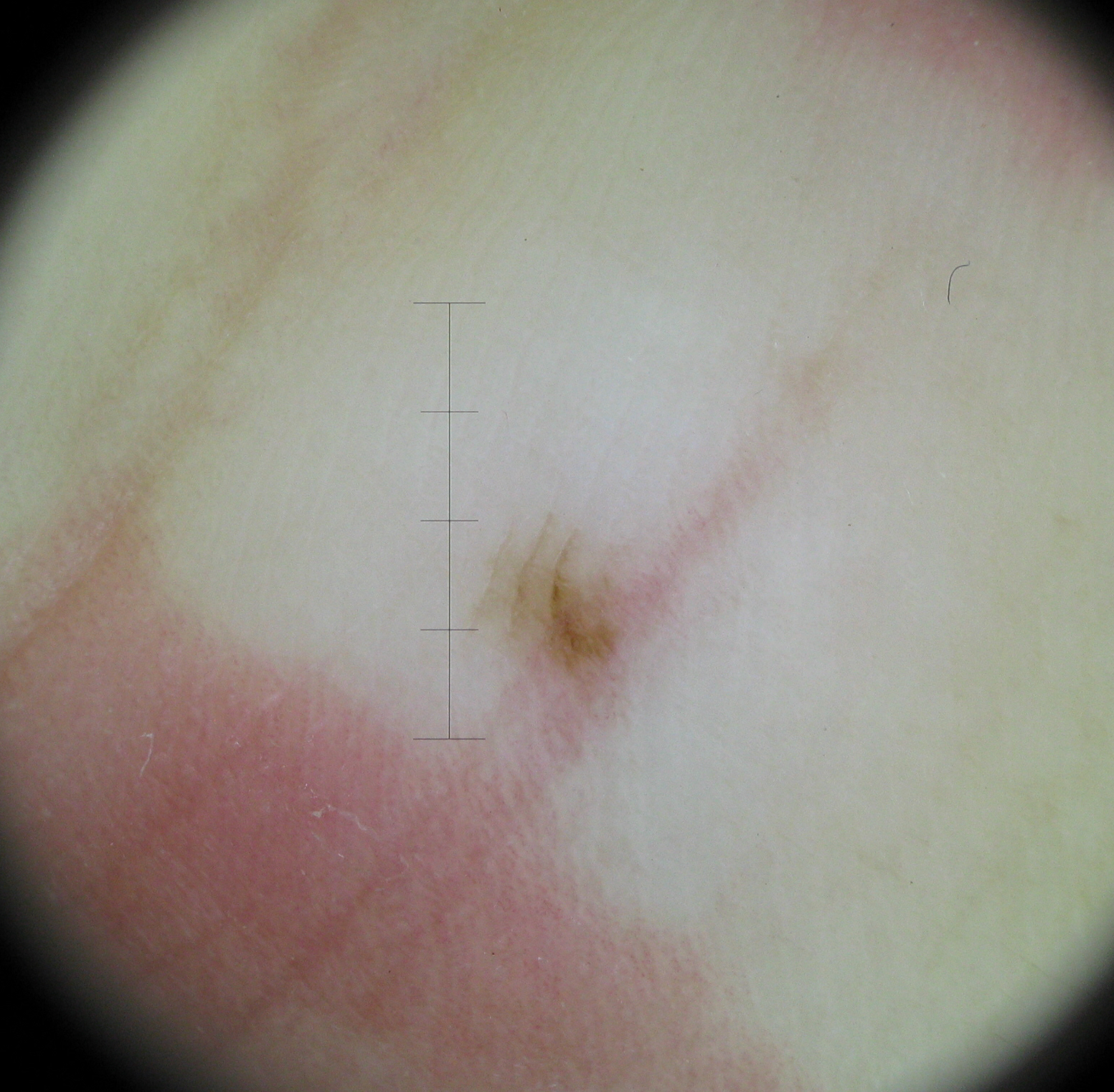Labeled as an acral junctional nevus.